A dermoscopic image of a skin lesion.
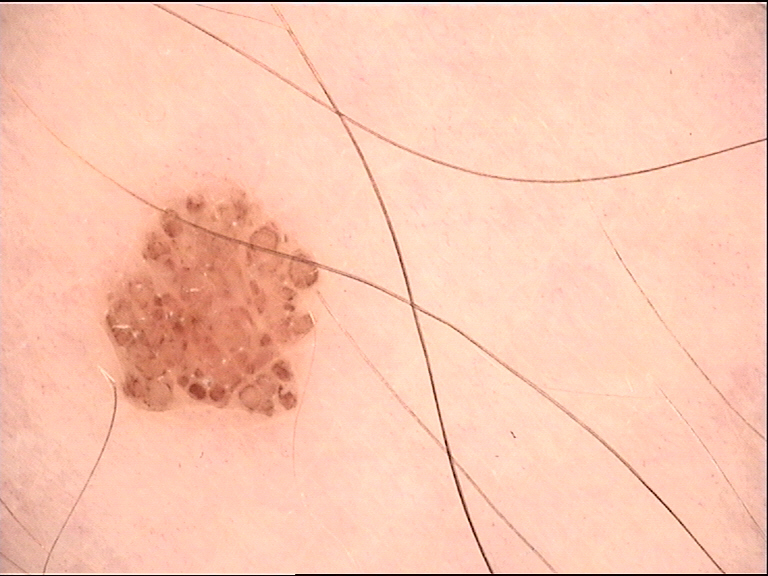lesion type: banal, diagnostic label: compound nevus (expert consensus).